A dermoscopic photograph of a skin lesion: 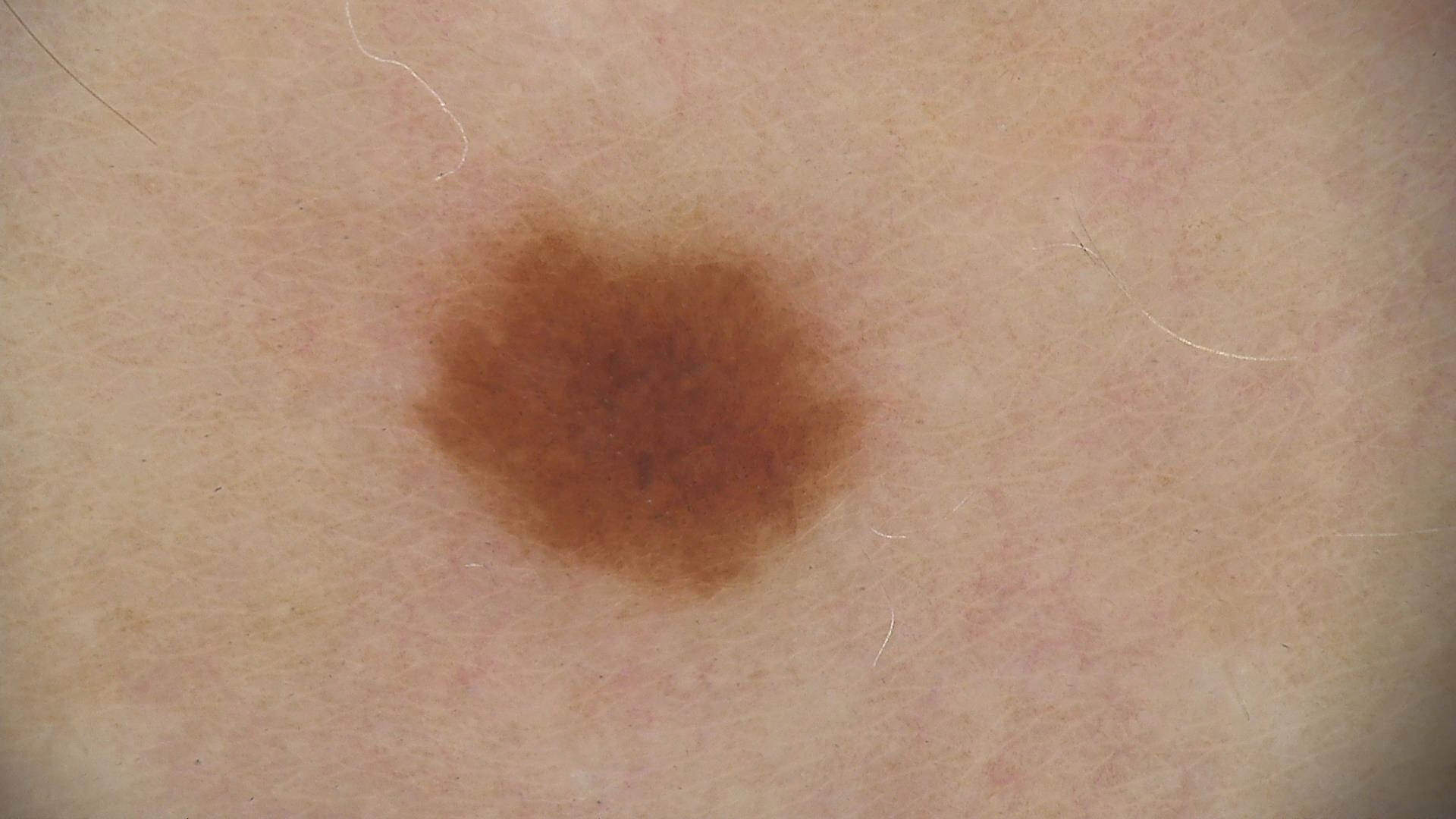Impression: Diagnosed as a benign lesion — a dysplastic junctional nevus.